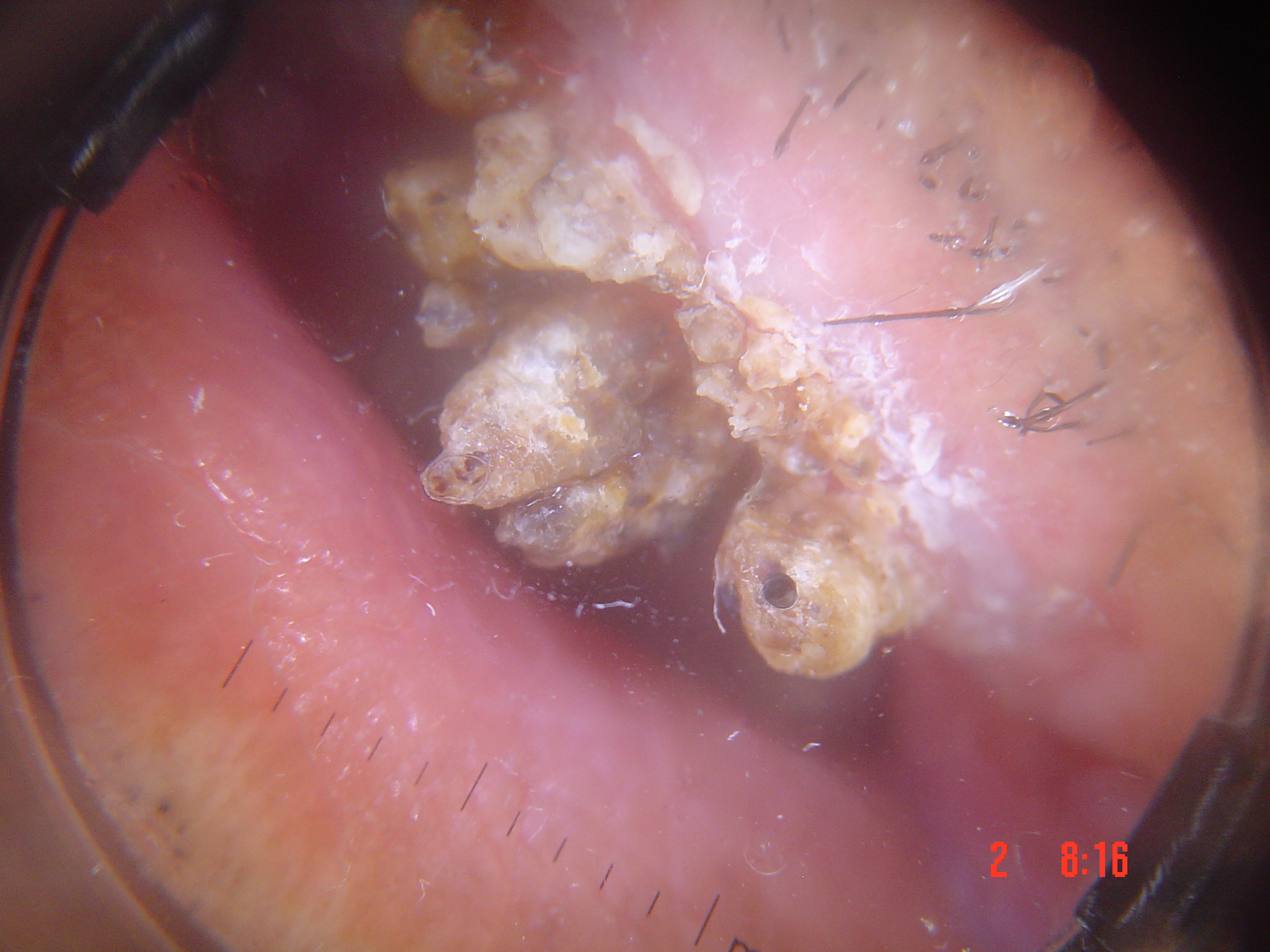Q: What did the workup show?
A: squamous cell carcinoma (biopsy-proven)